Female subject, age 18–29 · reported lesion symptoms include itching · no associated systemic symptoms reported · the condition has been present for less than one week · the patient considered this a rash · this image was taken at an angle · texture is reported as raised or bumpy.
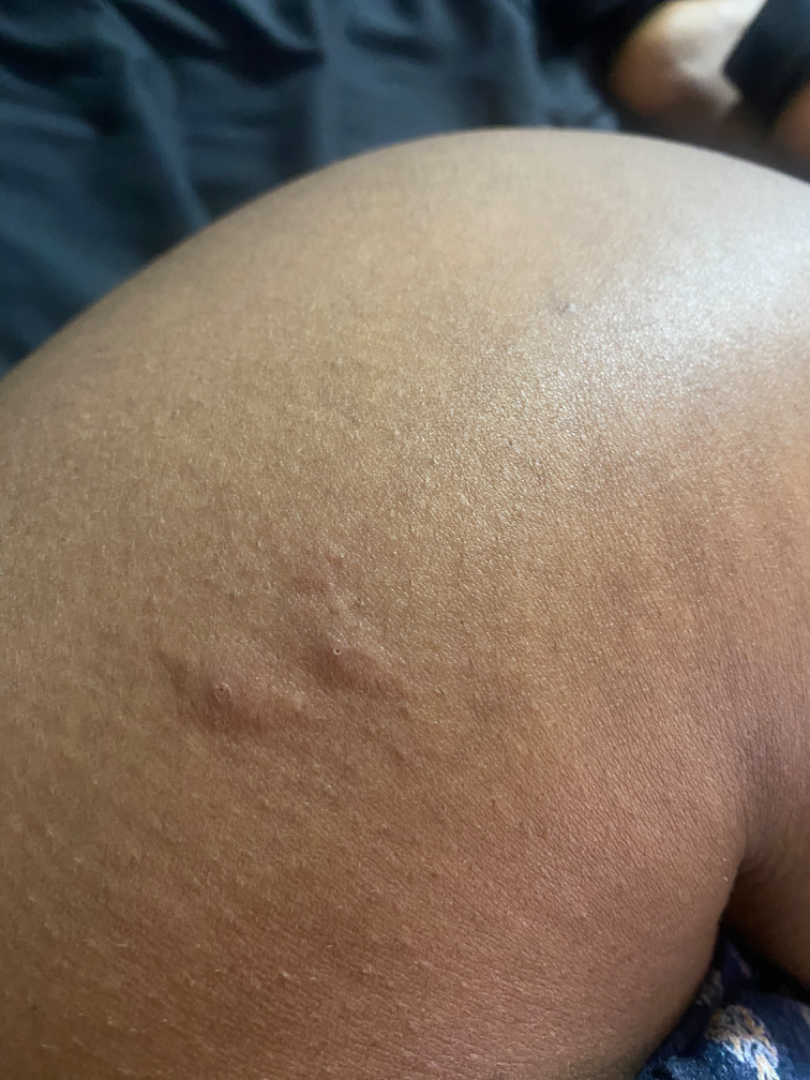Insect Bite (considered); Cyst (considered); Adnexal neoplasm (less likely); Urticaria (less likely); Eczema (less likely).